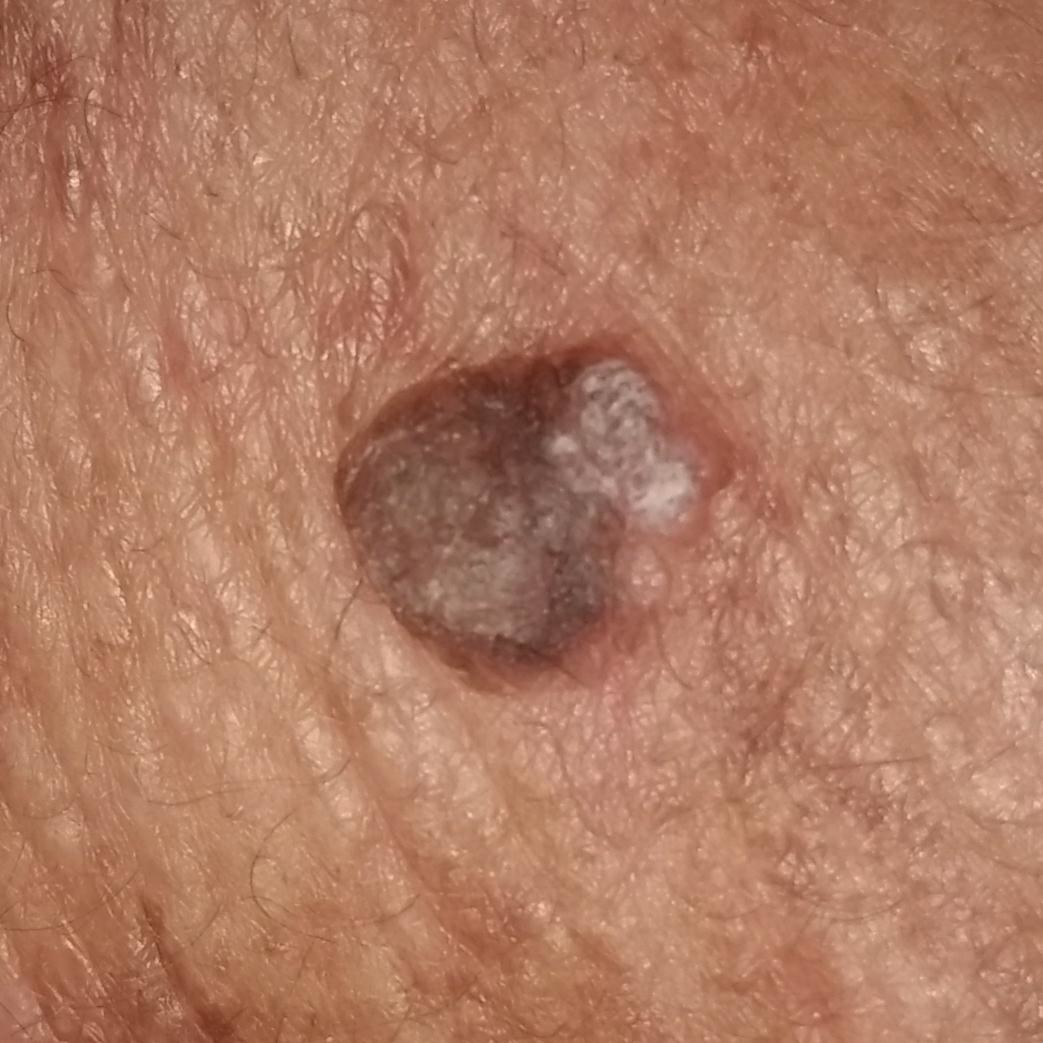- symptoms · elevation, itching / no pain, no change in appearance
- diagnosis · seborrheic keratosis (clinical consensus)